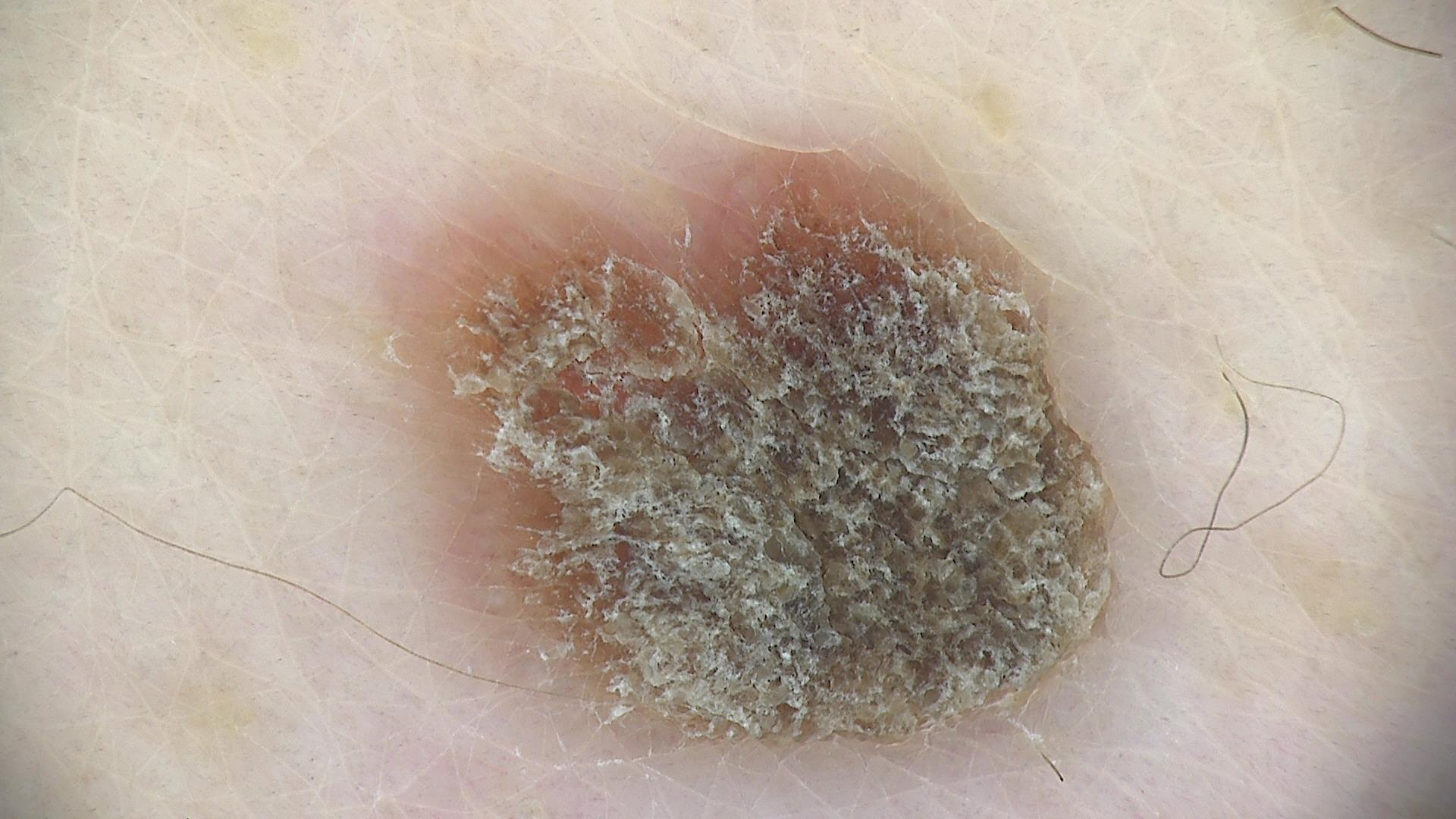image: dermoscopy, class: seborrheic keratosis (expert consensus).